Dermoscopy of a skin lesion:
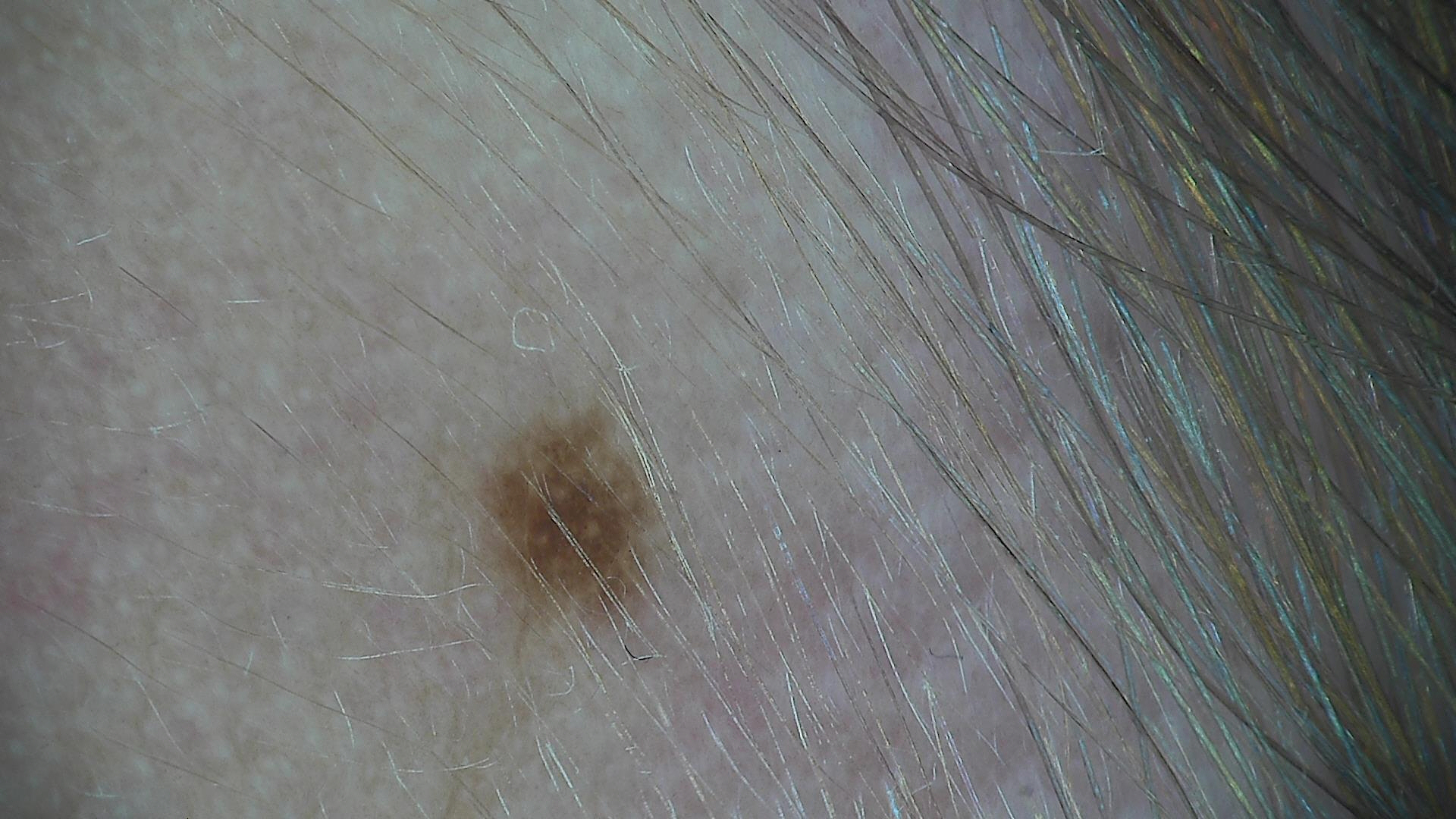diagnostic label — junctional nevus (expert consensus)